Dermoscopy of a skin lesion:
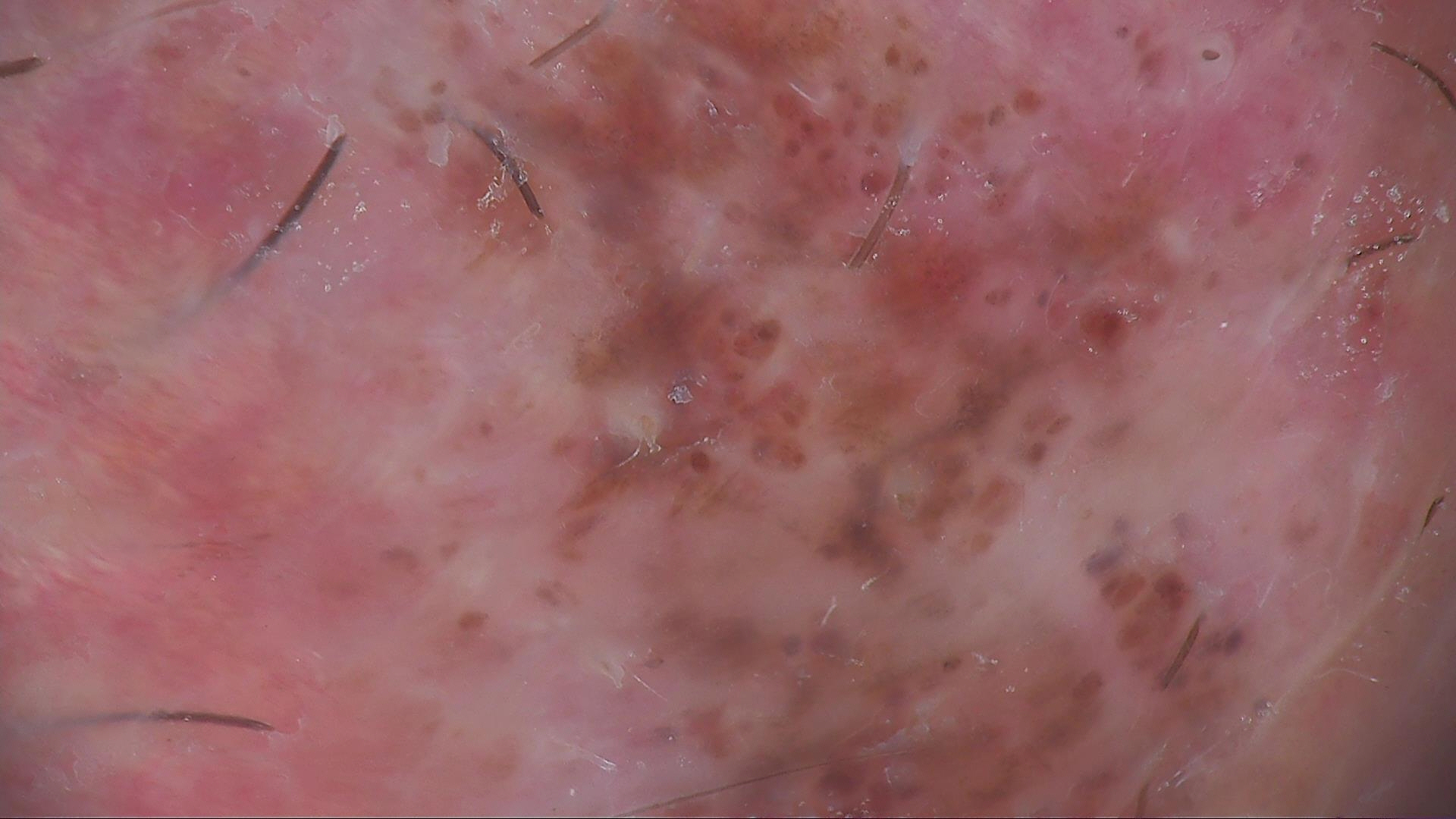Consistent with a banal lesion — a dermal nevus.